Dermoscopy of a skin lesion.
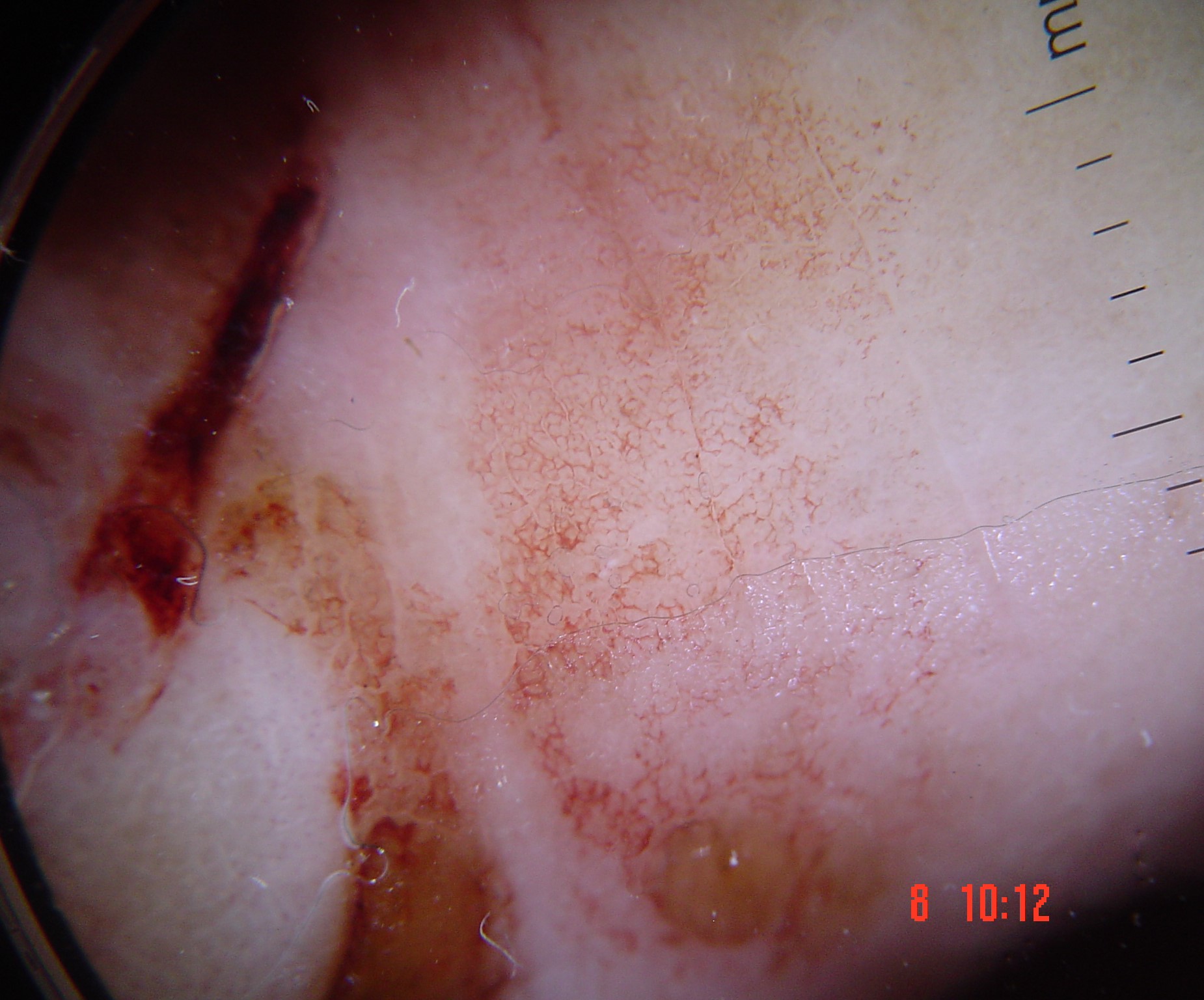Confirmed on histopathology as a skin cancer — an acral nodular melanoma.